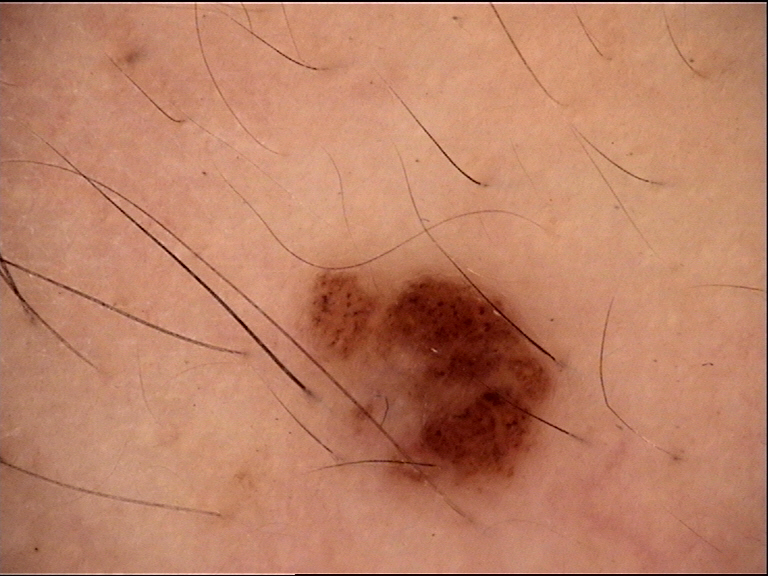A dermoscopic close-up of a skin lesion. Labeled as a banal lesion — a compound nevus.